Dermoscopy of a skin lesion.
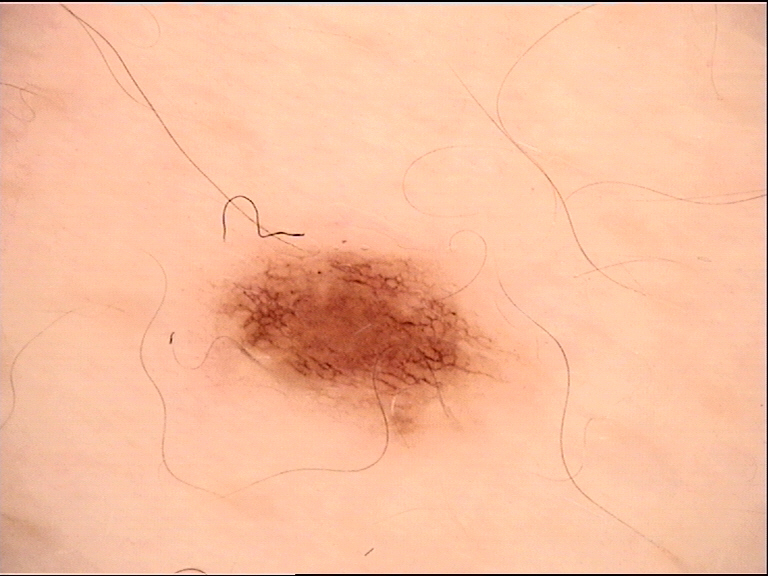Labeled as a dysplastic junctional nevus.